An image taken at a distance. The contributor notes the lesion is rough or flaky. The contributor notes associated shortness of breath, joint pain and fatigue. The affected area is the leg. Female contributor, age 40–49. The patient did not report lesion symptoms: 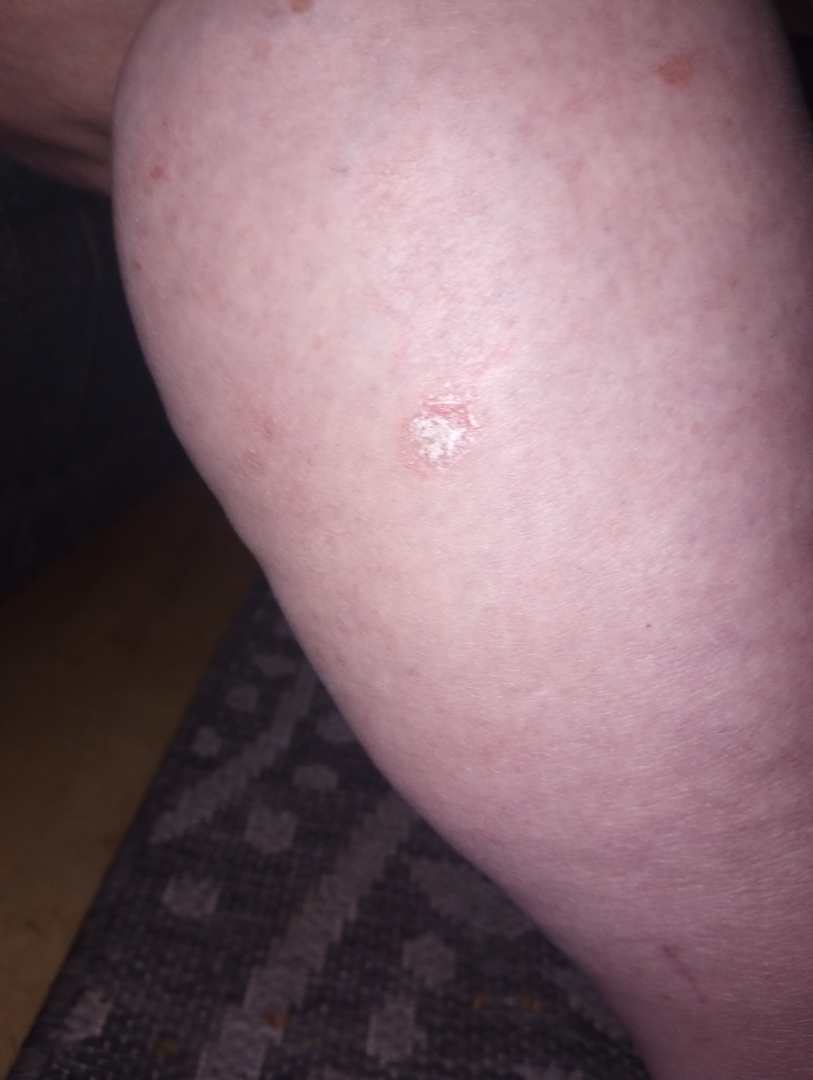Assessment: SCC/SCCIS (leading); SK/ISK (possible).